Dermoscopy of a skin lesion.
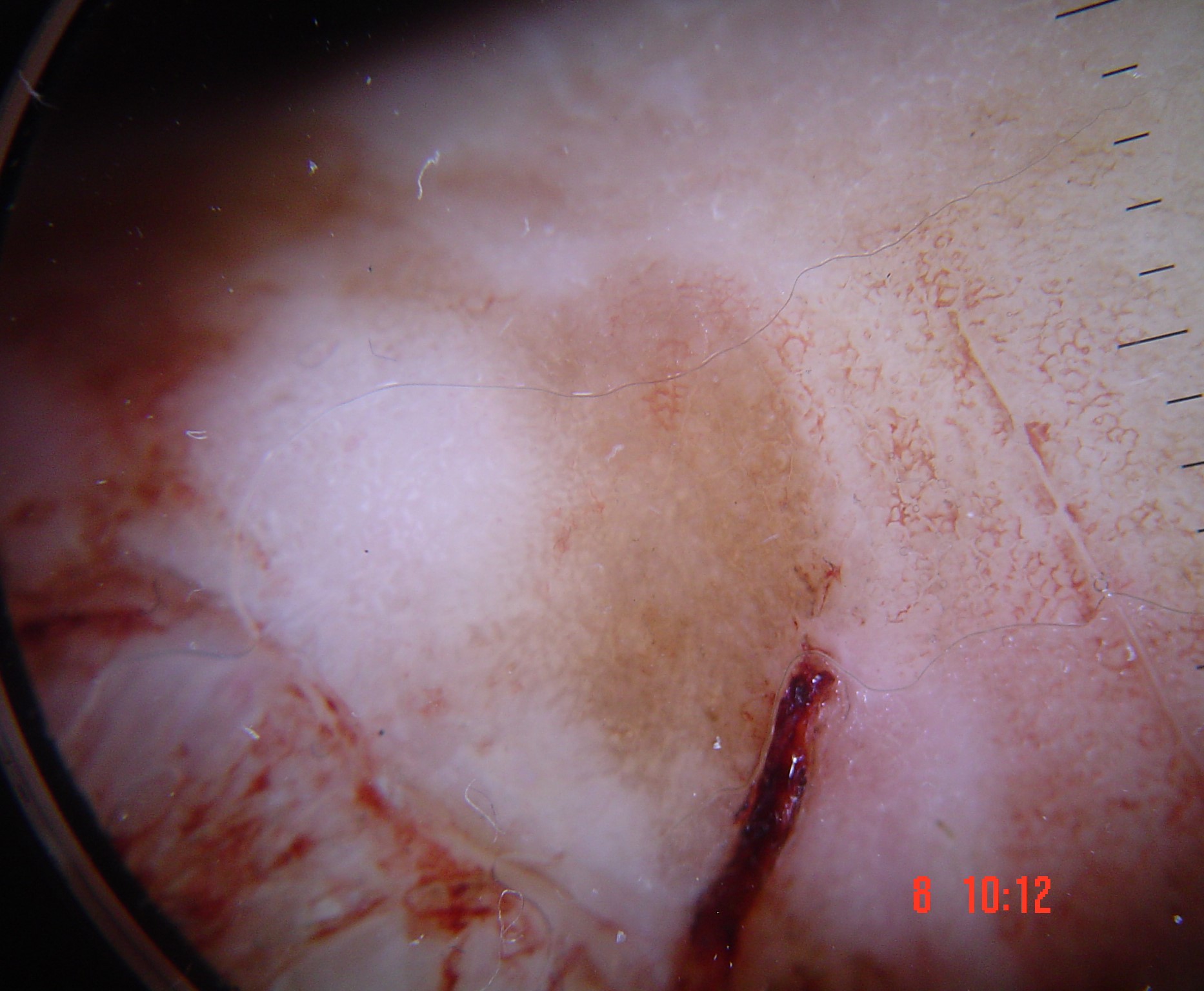class — acral nodular melanoma (biopsy-proven)